The subject is a male aged 30–39; the lesion involves the leg; an image taken at an angle — 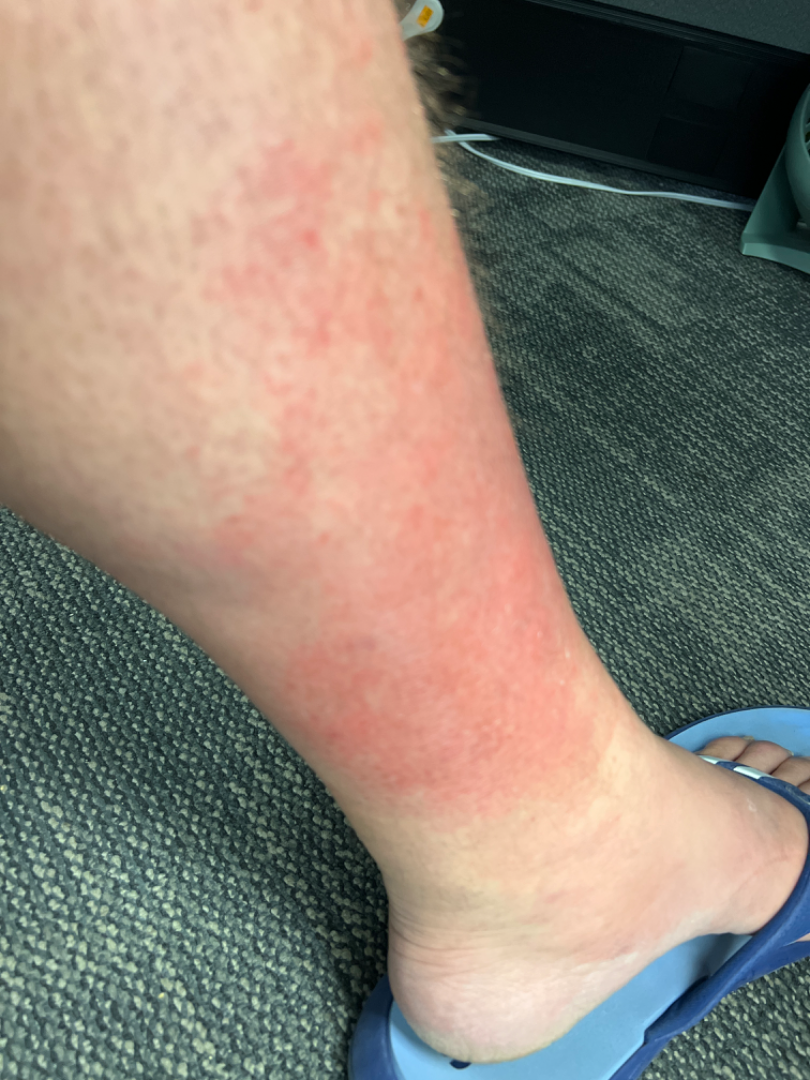Q: Patient's own categorization?
A: a rash
Q: Constitutional symptoms?
A: joint pain
Q: How does the lesion feel?
A: rough or flaky and flat
Q: Duration?
A: less than one week
Q: What is the differential diagnosis?
A: consistent with Stasis Dermatitis